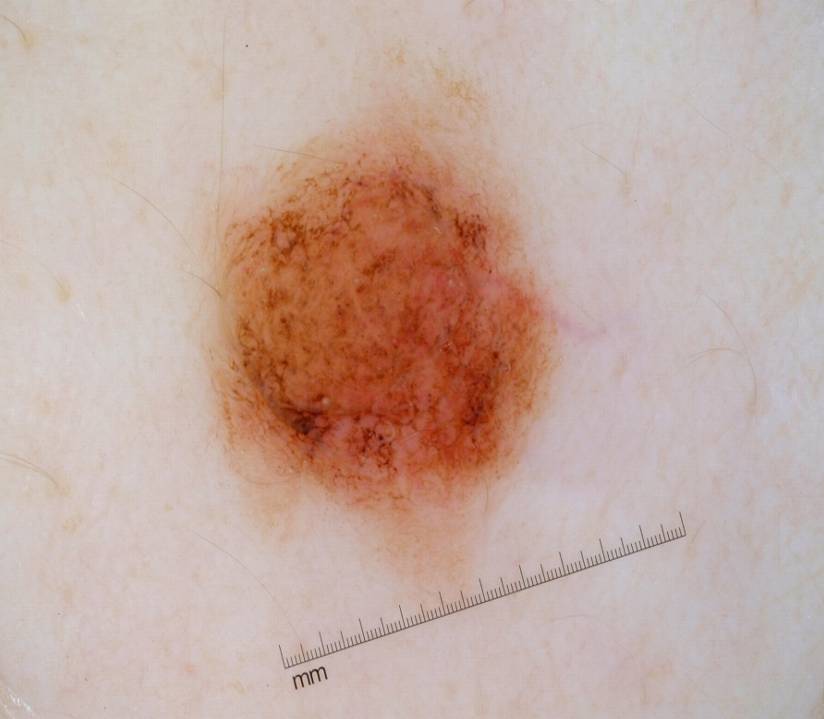image type=dermoscopy of a skin lesion
size=~21% of the field
dermoscopic pattern=globules
bounding box=204 68 559 581
impression=a melanocytic nevus